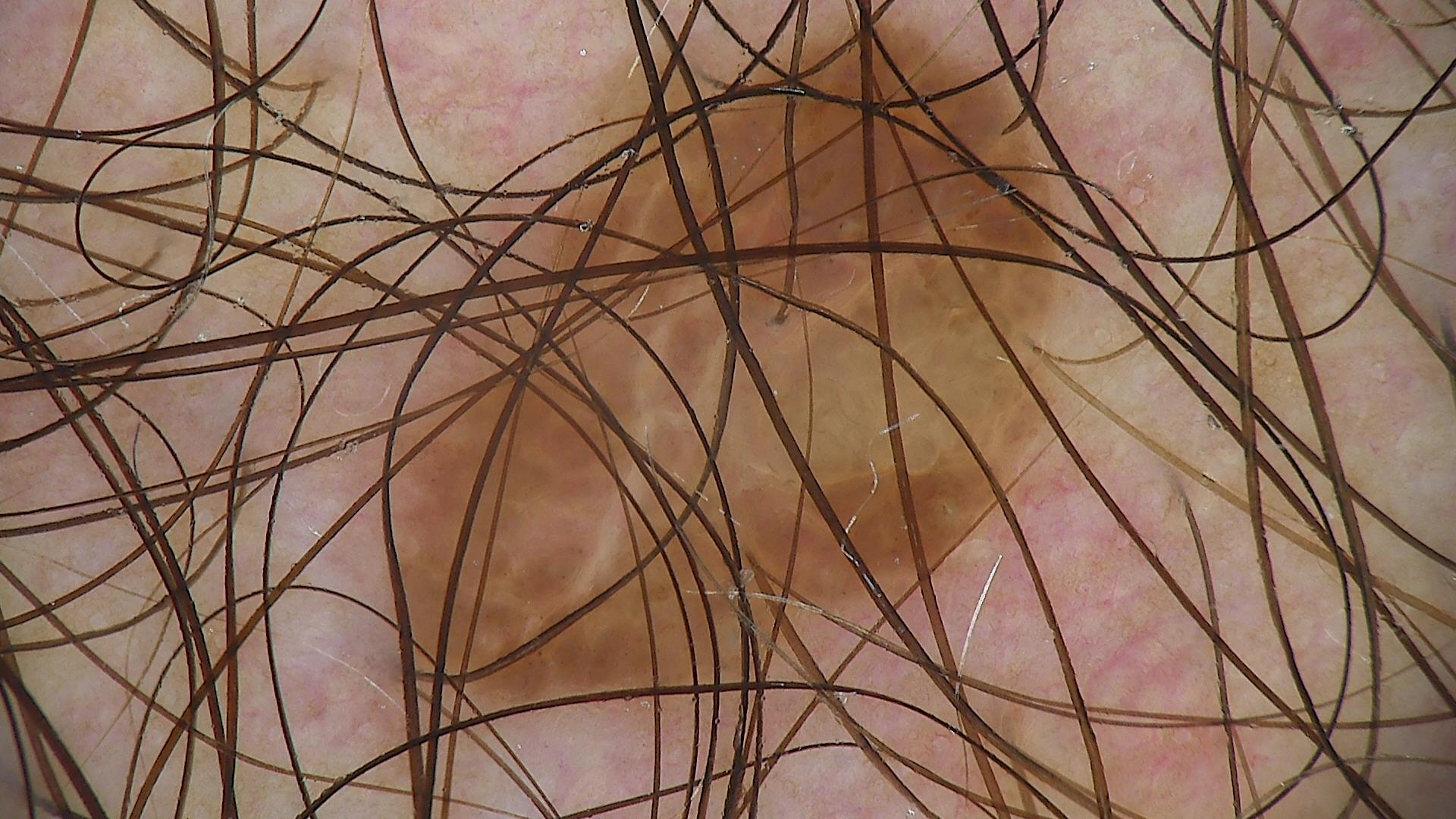image: dermatoscopy
diagnosis: compound nevus (expert consensus)